Dermoscopy of a skin lesion.
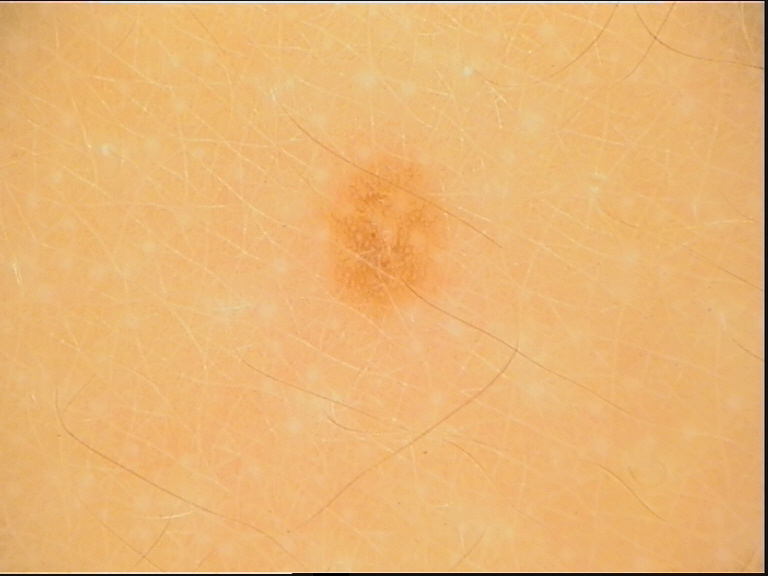Consistent with a benign lesion — a dysplastic junctional nevus.